The patient is FST II; a female patient approximately 30 years of age; a contact-polarized dermoscopy image of a skin lesion.
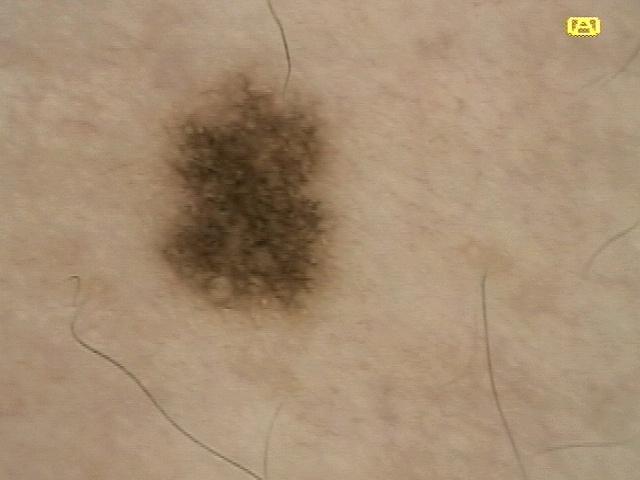| field | value |
|---|---|
| impression | Nevus |